A dermatoscopic image of a skin lesion.
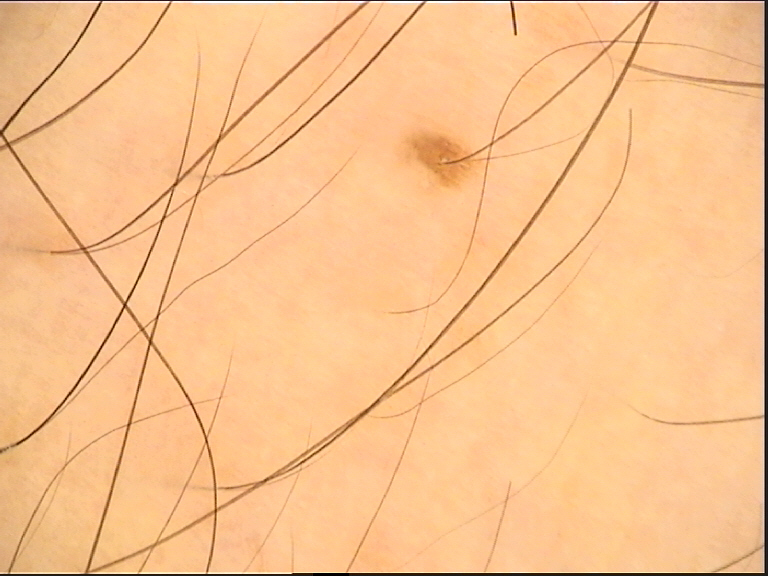Findings:
The architecture is that of a banal lesion.
Conclusion:
The diagnostic label was a junctional nevus.